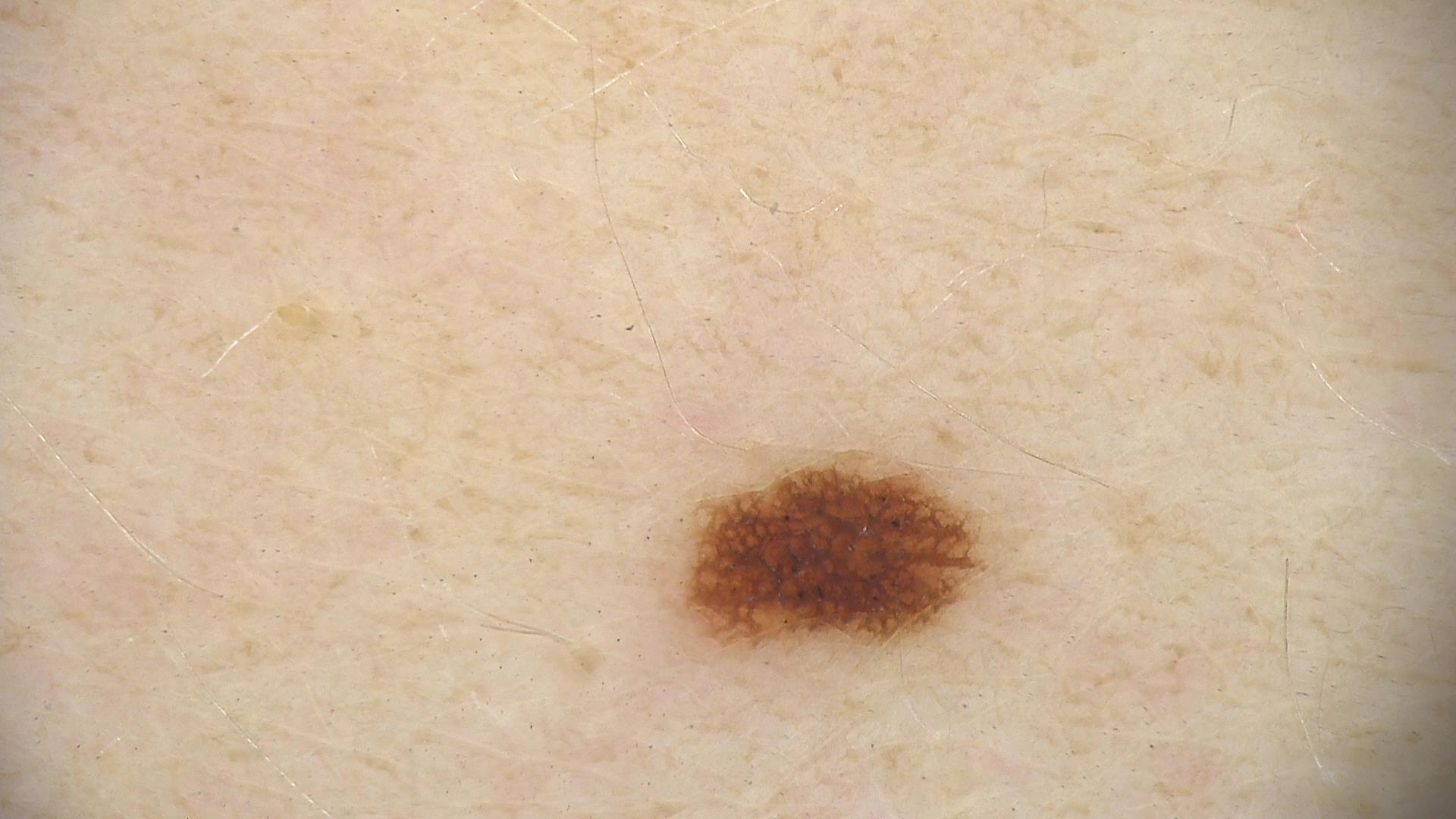A dermoscopic image of a skin lesion.
Classified as a benign lesion — a dysplastic junctional nevus.